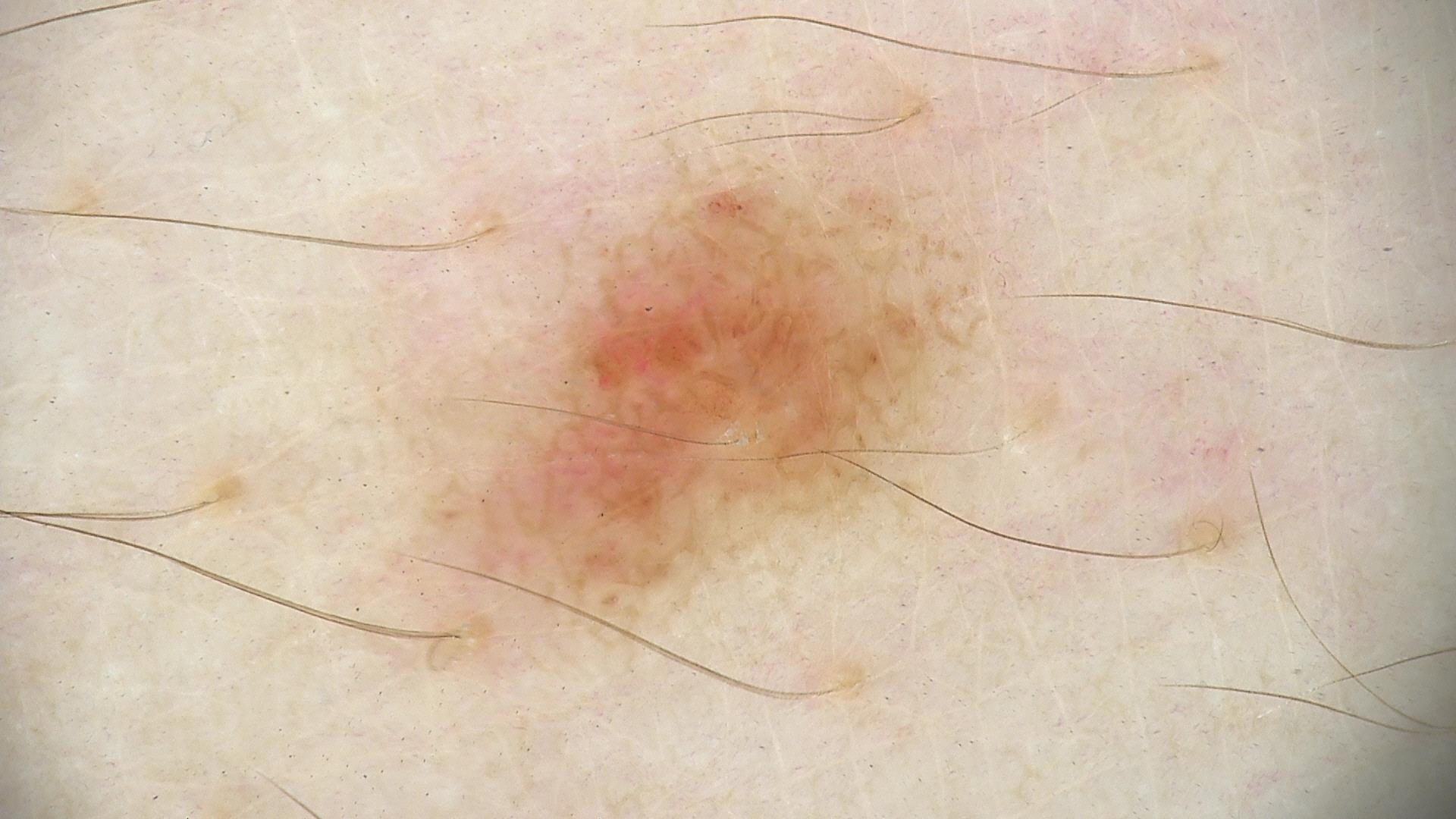Q: What kind of image is this?
A: dermoscopy
Q: What is this lesion?
A: dysplastic junctional nevus (expert consensus)